This is a dermoscopic photograph of a skin lesion — 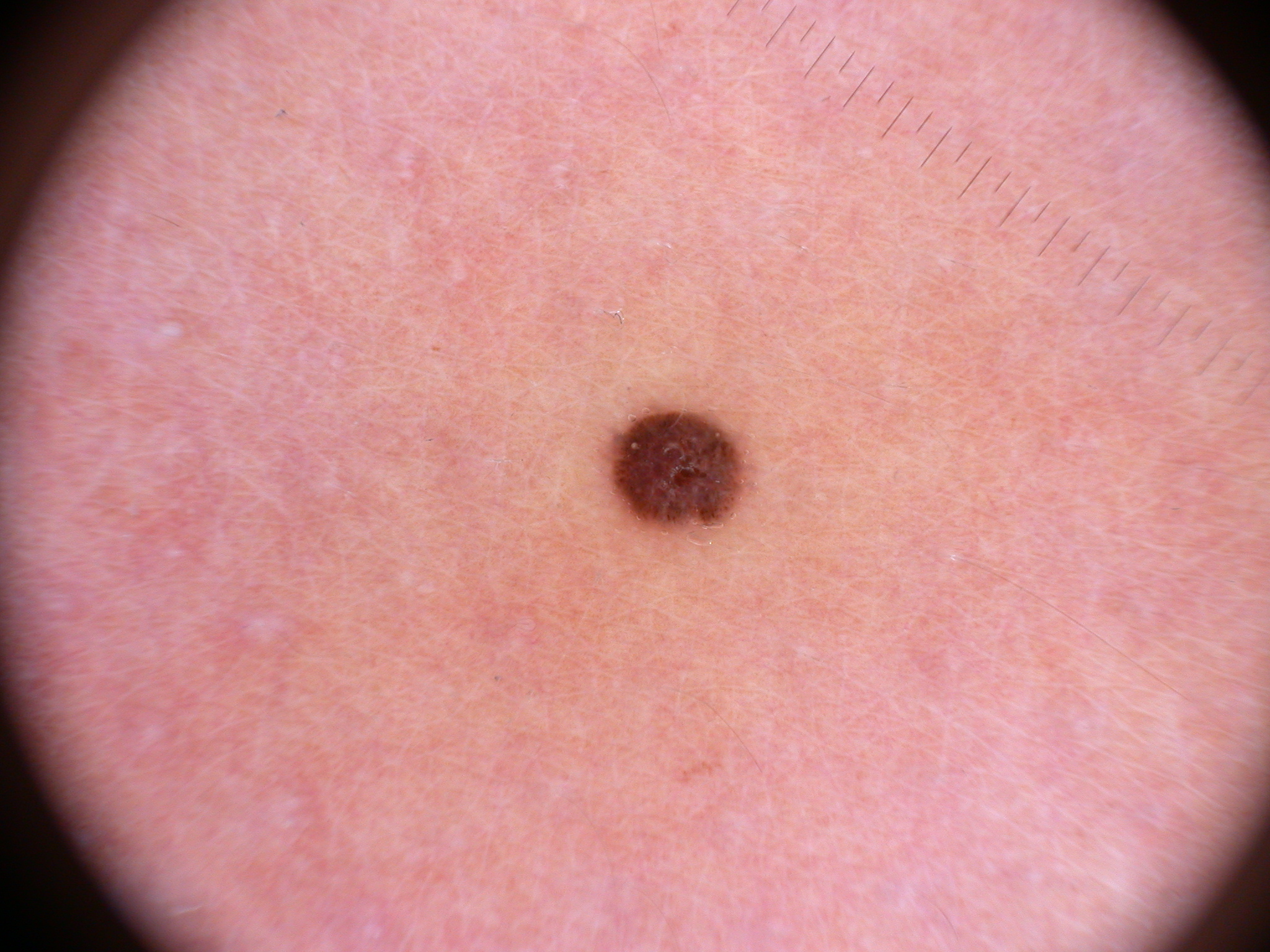The lesion takes up about 1% of the image. Dermoscopy demonstrates milia-like cysts. With coordinates (x1, y1, x2, y2), lesion location: bbox=[610, 410, 744, 531]. The clinical diagnosis was a melanocytic nevus, a benign skin lesion.